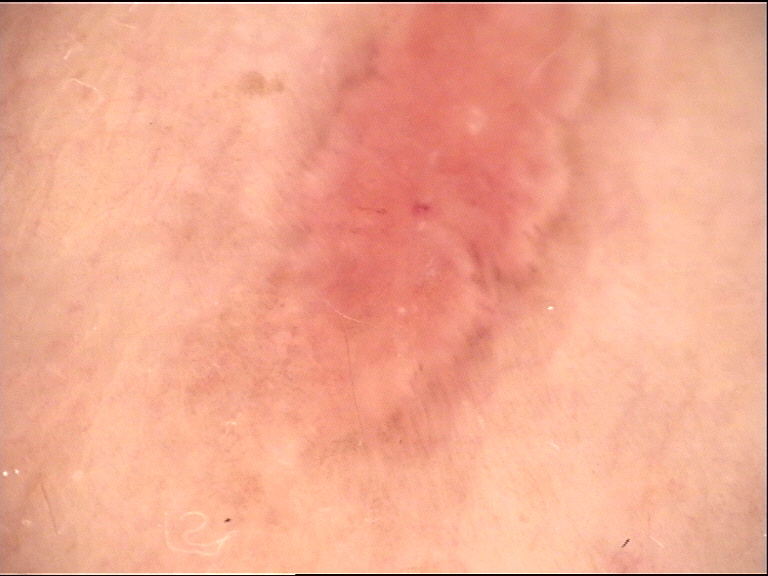image: dermatoscopy, category: keratinocytic, diagnosis: basal cell carcinoma (biopsy-proven).